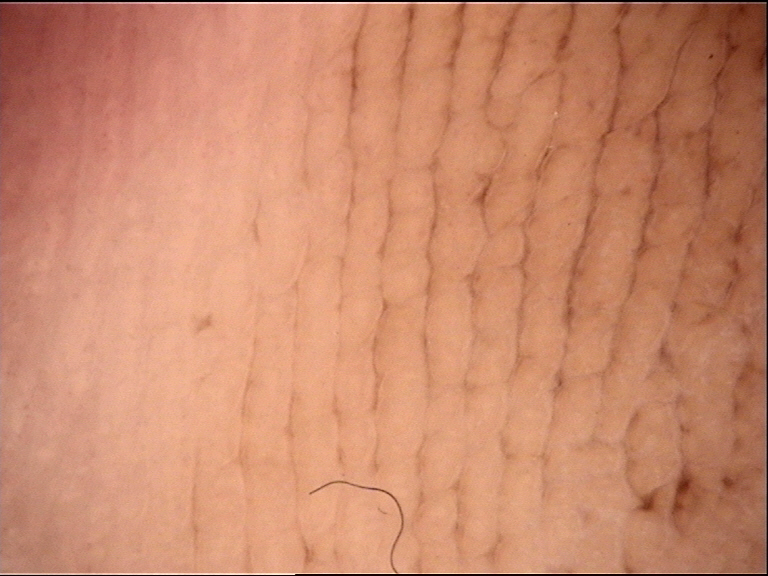Findings: The morphology is that of a banal lesion. Impression: The diagnosis was an acral junctional nevus.